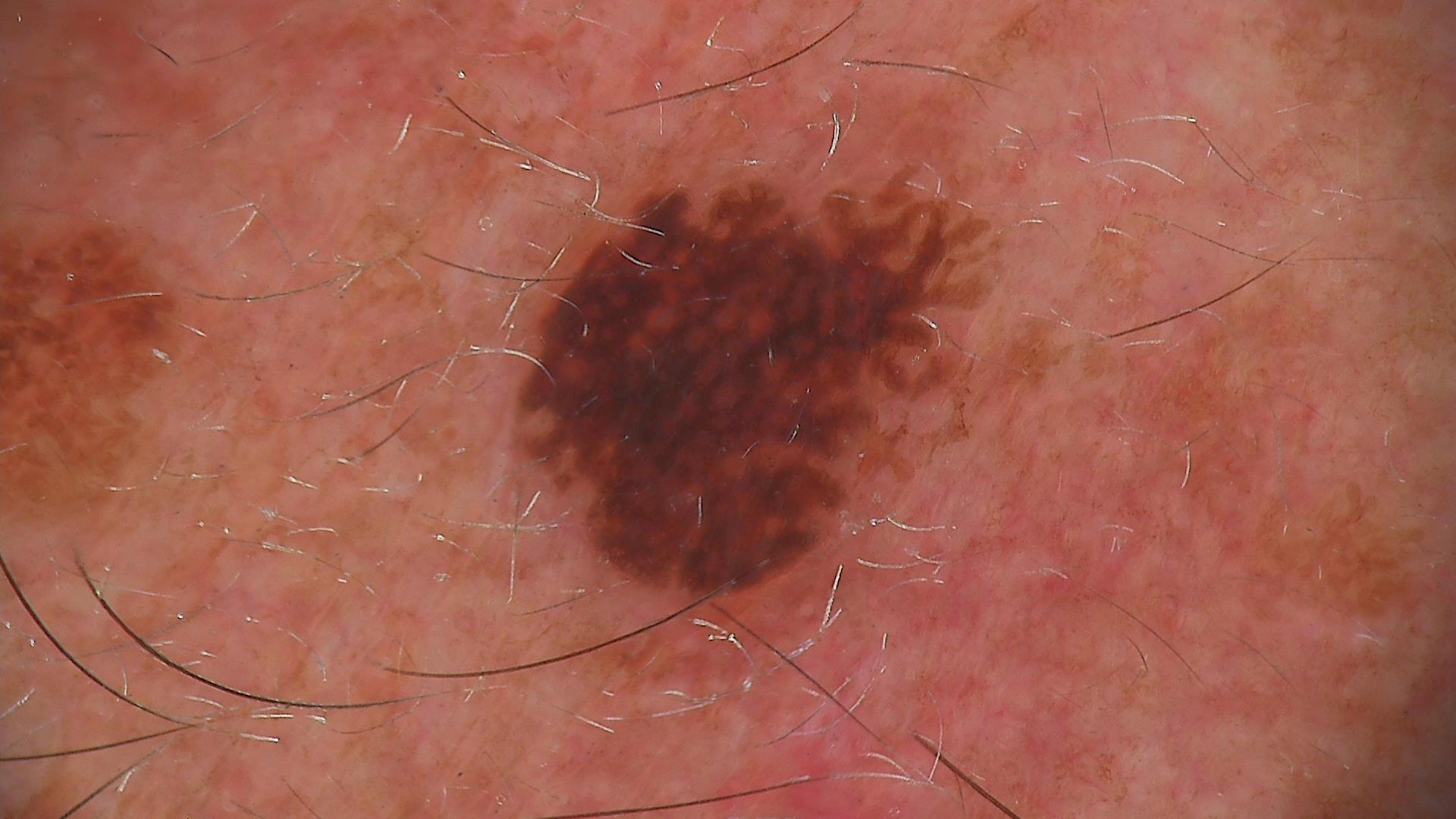A dermatoscopic image of a skin lesion.
Labeled as a keratinocytic lesion — a seborrheic keratosis.